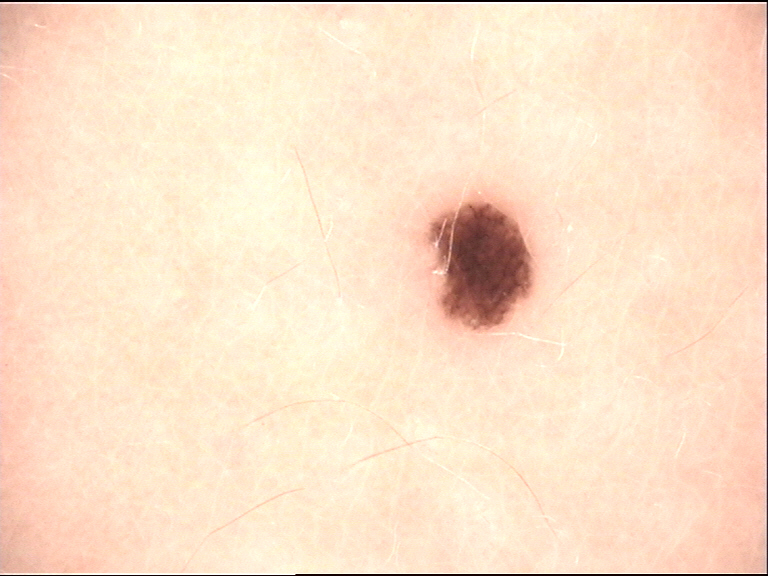Summary:
A dermoscopy image of a single skin lesion.
Impression:
Diagnosed as a banal lesion — a junctional nevus.